The patient notes itching and burning. The affected area is the leg. Texture is reported as raised or bumpy and rough or flaky. The condition has been present for three to twelve months. Close-up view. The patient described the issue as a rash: 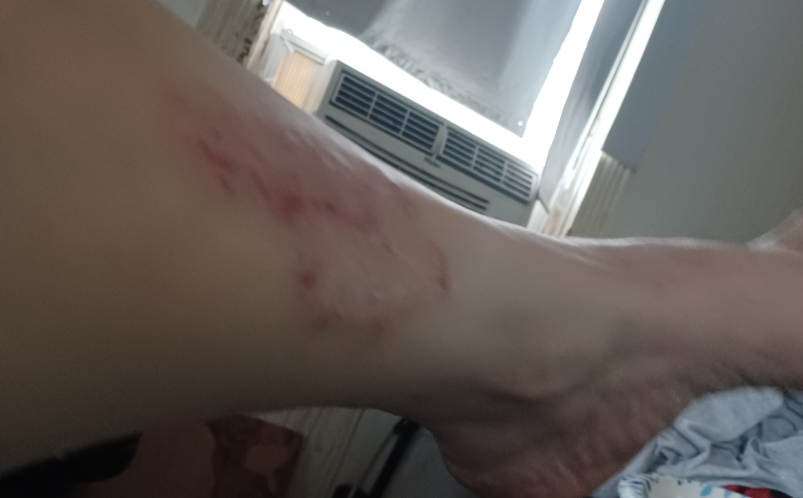Notes:
• assessment: ungradable on photographic review